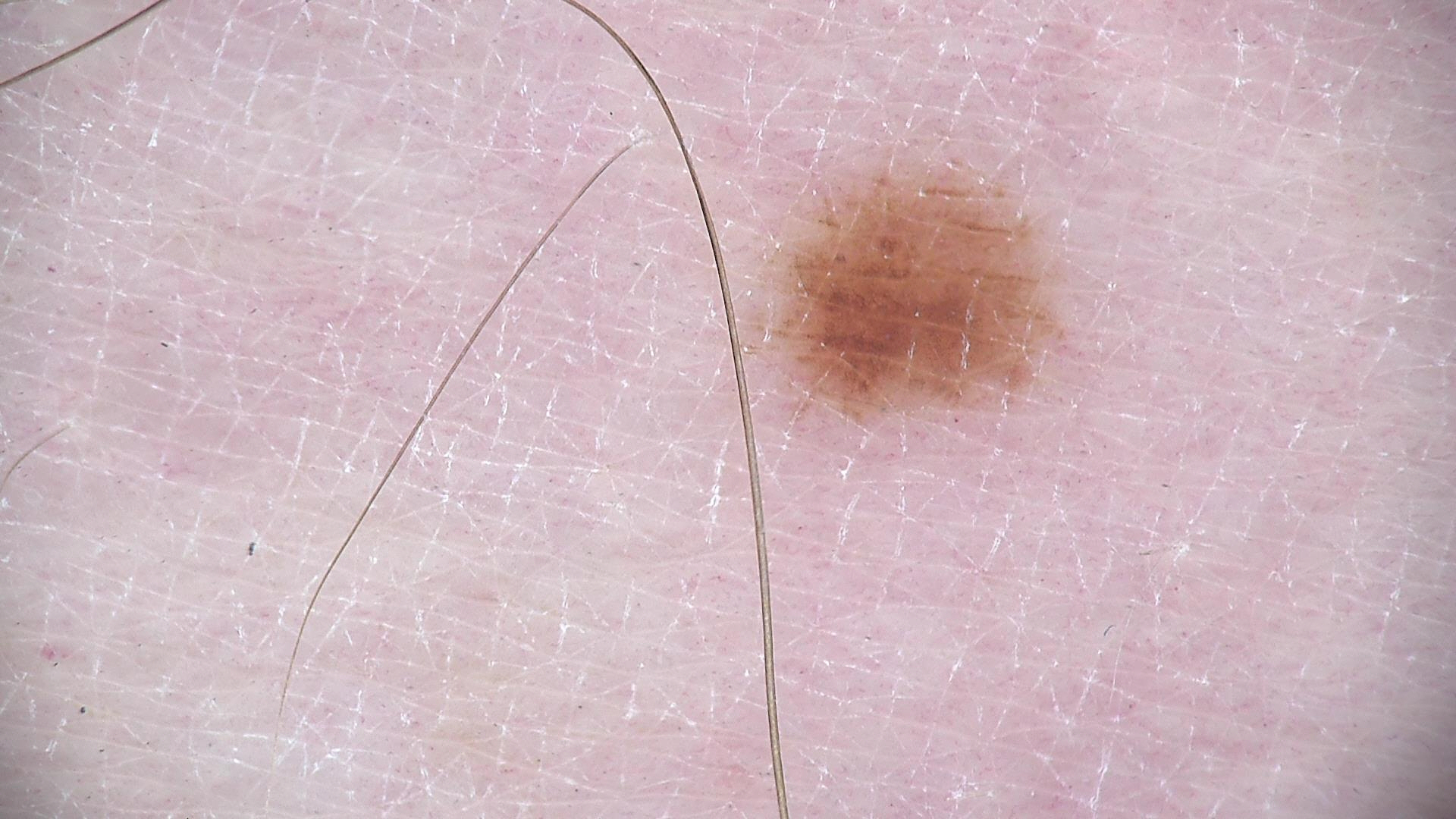Impression: Consistent with a dysplastic junctional nevus.